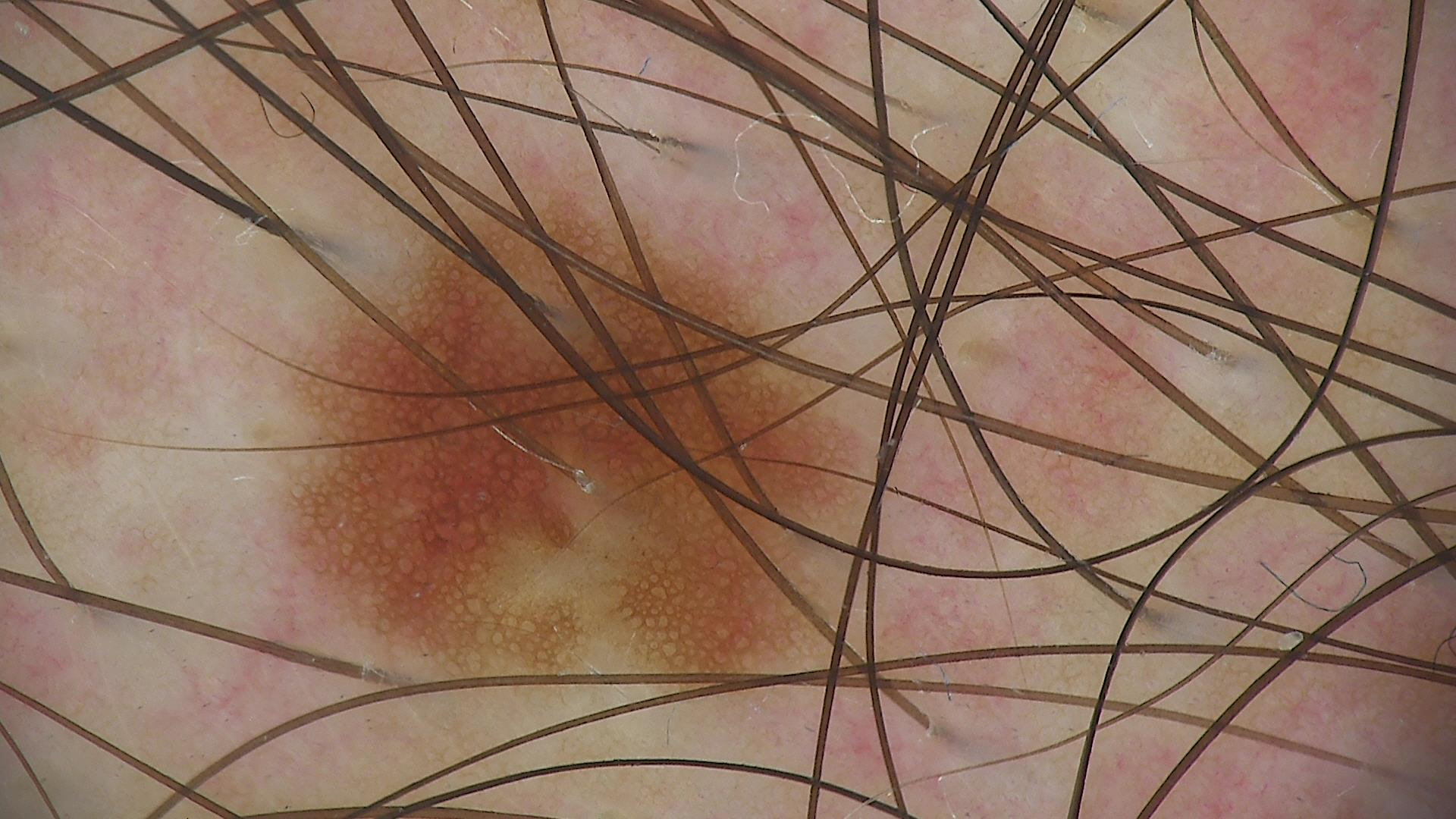The diagnosis was a junctional nevus.